A dermoscopy image of a skin lesion · collected as part of a research study, without a referral diagnosis · a female subject 50 years of age · a moderate number of moles by the patient's own estimate.
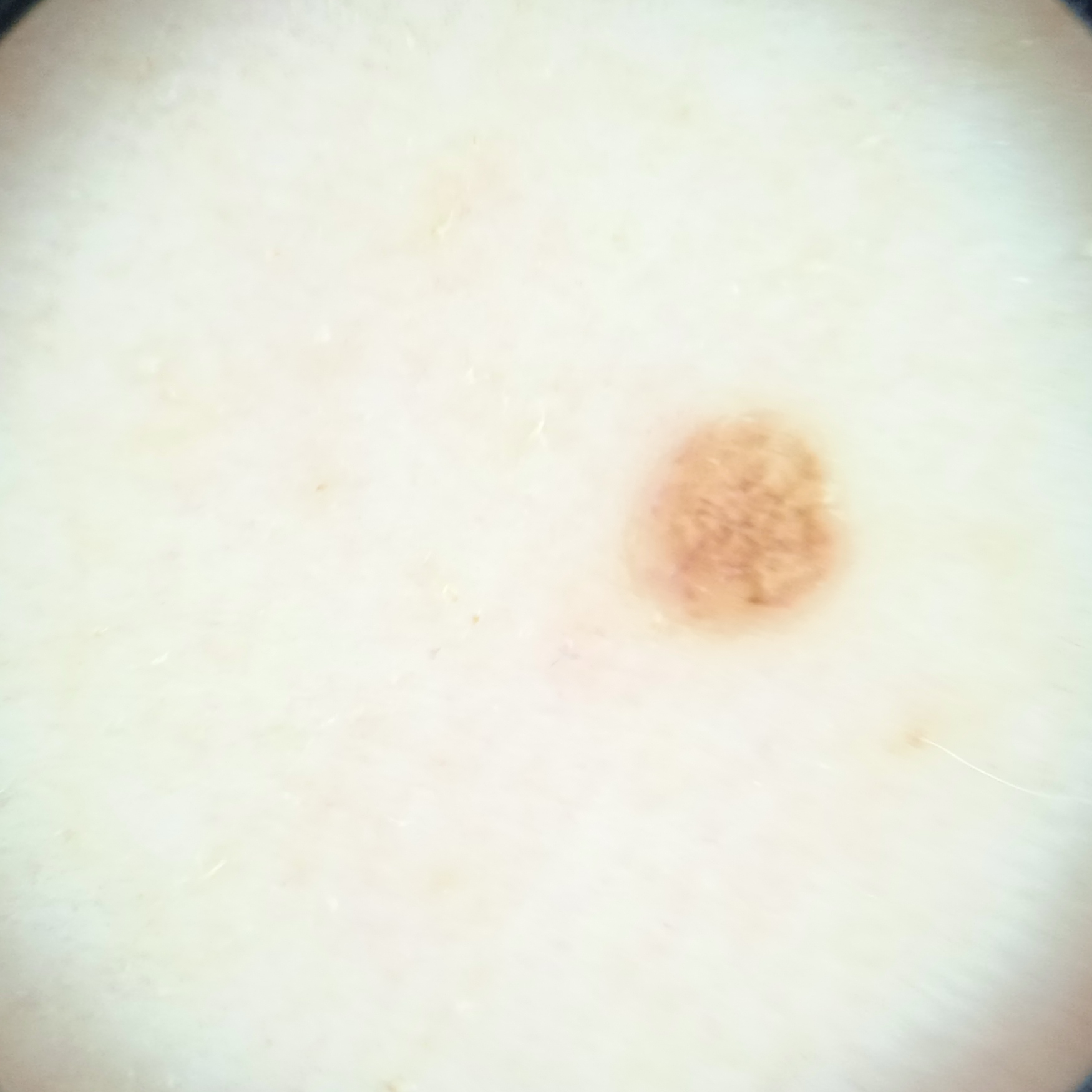size = 2.2 mm
diagnostic label = melanocytic nevus (dermatologist consensus)